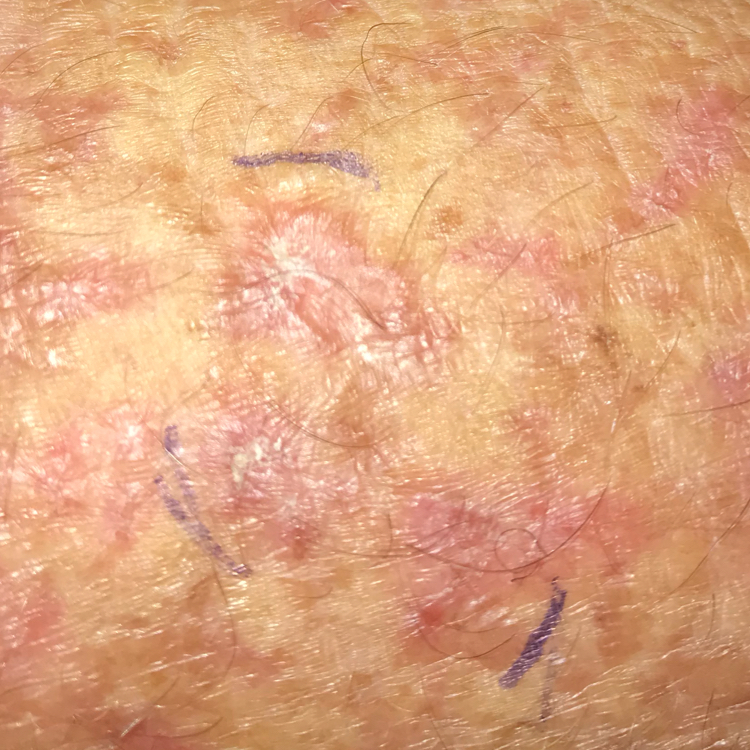A patient in their late 60s.
Per patient report, the lesion itches and is elevated, but has not changed and has not bled.
Clinically diagnosed as a premalignant lesion — an actinic keratosis.